A dermoscopic close-up of a skin lesion.
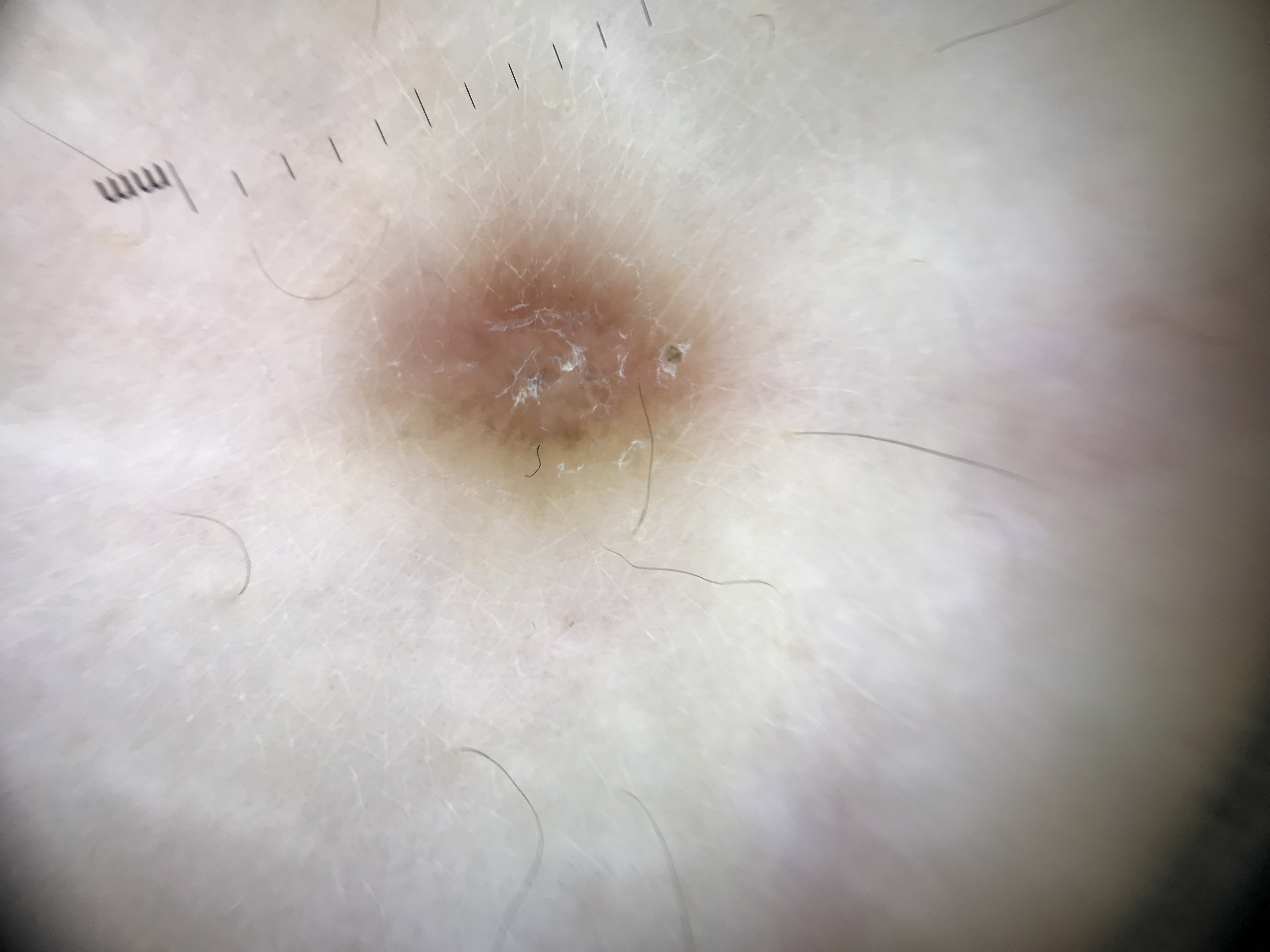Consistent with a fibro-histiocytic lesion — a dermatofibroma.